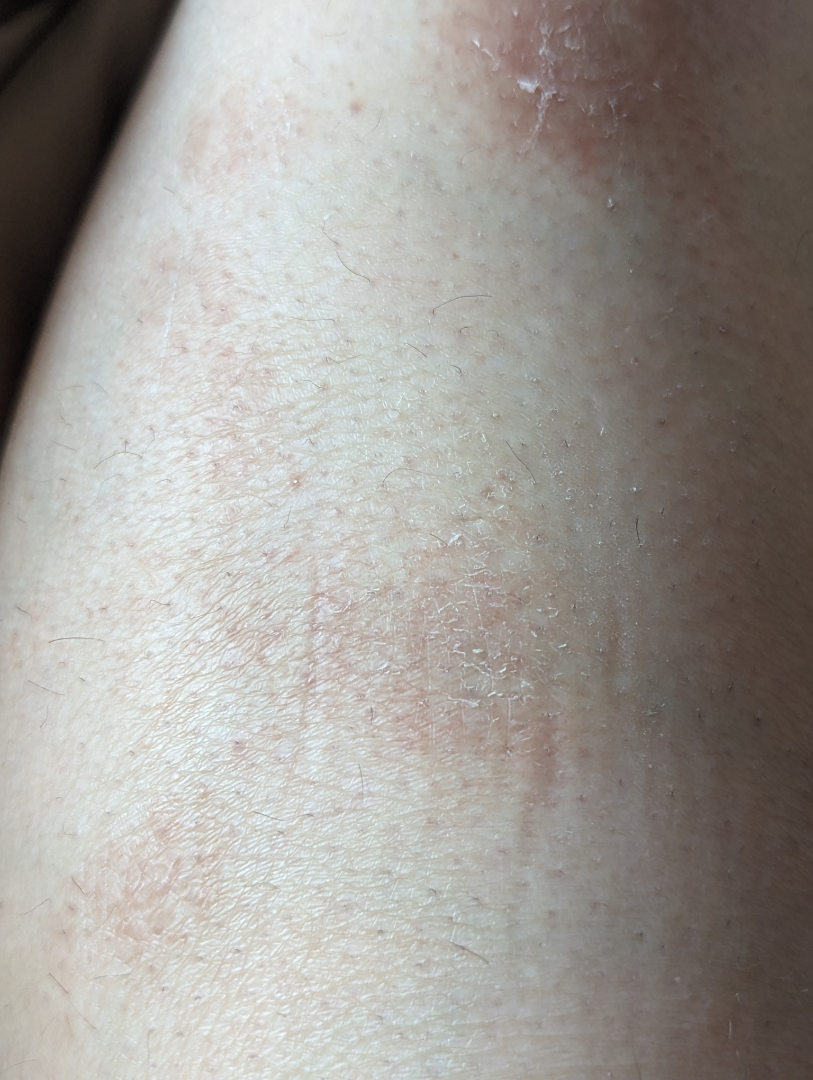An image taken at a distance. The affected area is the leg. The reviewing dermatologist's impression was: Pigmented purpuric eruption and Erythema nodosum were considered with similar weight.